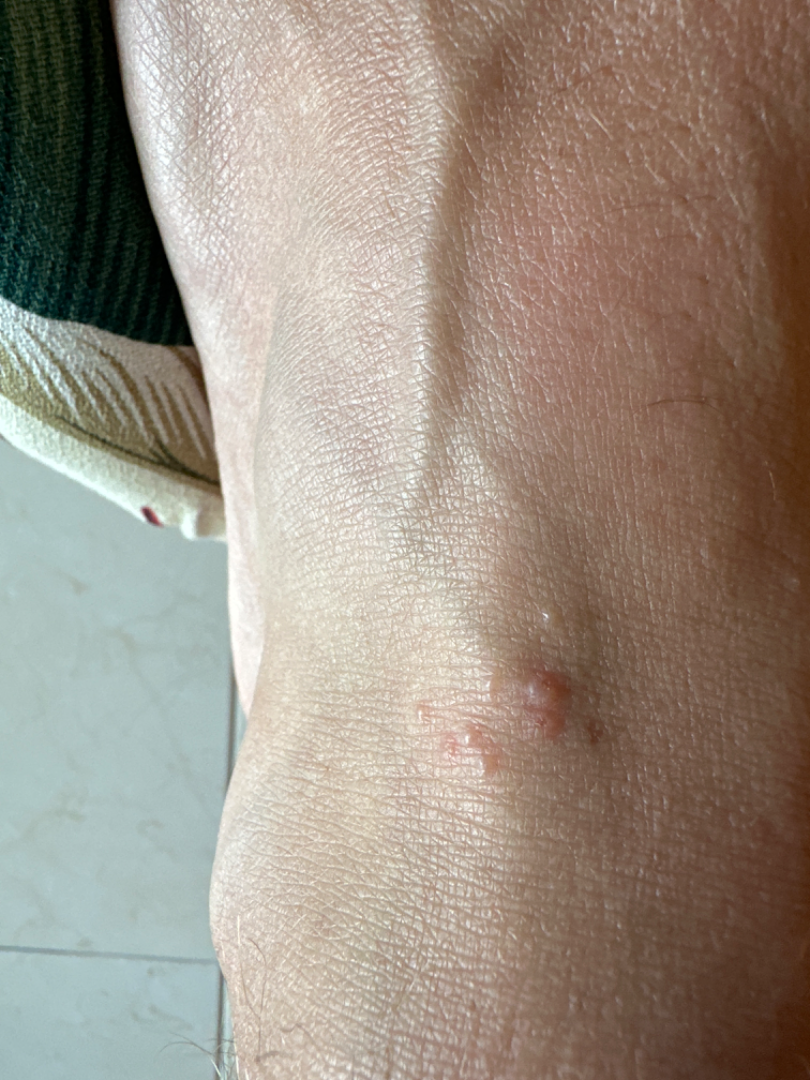The photograph is a close-up of the affected area. The contributor notes the lesion is raised or bumpy and fluid-filled. Skin tone: FST III; human graders estimated MST 1 or 2. The lesion involves the top or side of the foot, back of the hand and arm. No associated lesion symptoms were reported. No relevant systemic symptoms. The contributor notes the condition has been present for less than one week. In keeping with Allergic Contact Dermatitis.